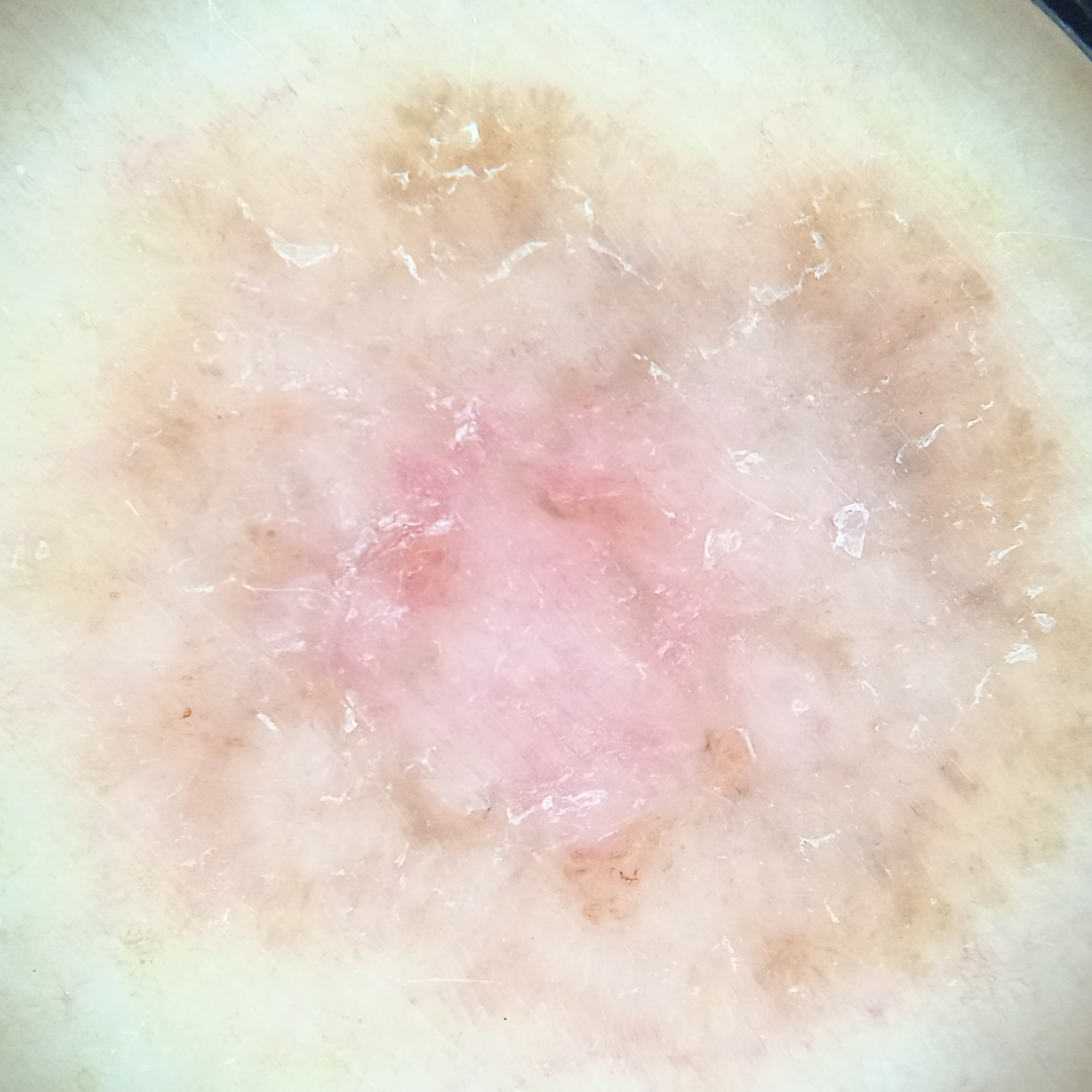{
  "risk_factors": {
    "positive": [
      "a personal history of cancer",
      "a personal history of skin cancer"
    ]
  },
  "patient": {
    "age": 60,
    "sex": "female"
  },
  "mole_burden": "few melanocytic nevi overall",
  "image": "dermoscopy",
  "sun_reaction": "skin tans without first burning",
  "lesion_location": "the torso",
  "lesion_size": {
    "diameter_mm": 13.2
  },
  "diagnosis": {
    "name": "basal cell carcinoma",
    "malignancy": "malignant"
  }
}